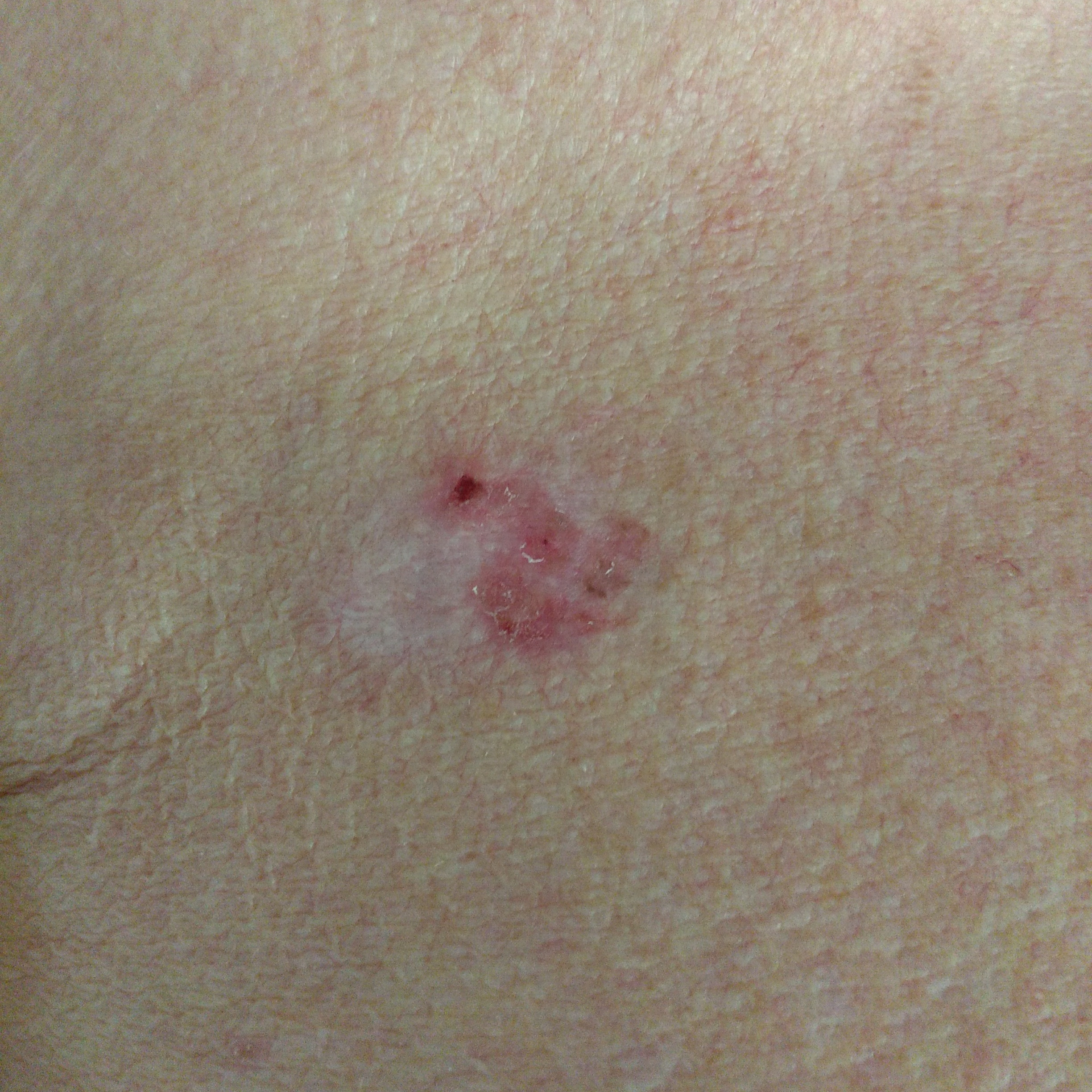exposure history: prior malignancy (patient or family)
FST: I
subject: male, age 80
image type: clinical photograph
site: the chest
diameter: 20x18 mm
patient-reported symptoms: elevation, growth, itching
diagnosis: basal cell carcinoma (biopsy-proven)